This is a dermoscopic photograph of a skin lesion · a female subject, aged 43-47 — 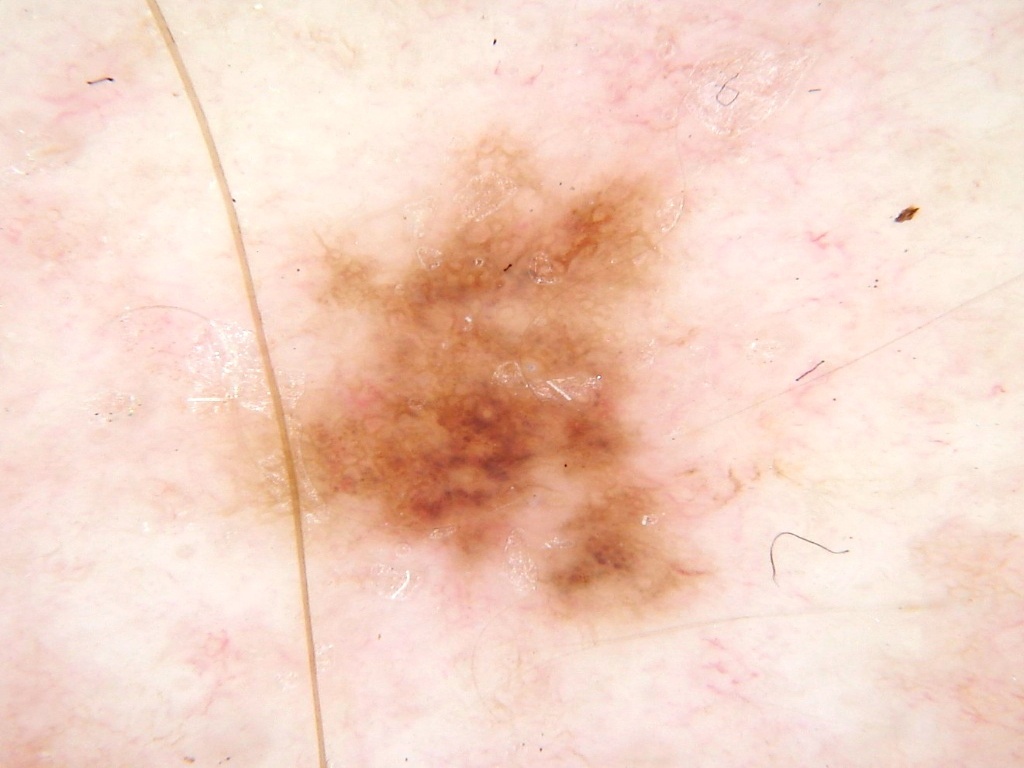As (left, top, right, bottom), the visible lesion spans 185/113/778/635.
Dermoscopic examination shows globules and pigment network, with no streaks, milia-like cysts, or negative network.
A moderately sized lesion.
Clinically diagnosed as a melanocytic nevus, a benign lesion.